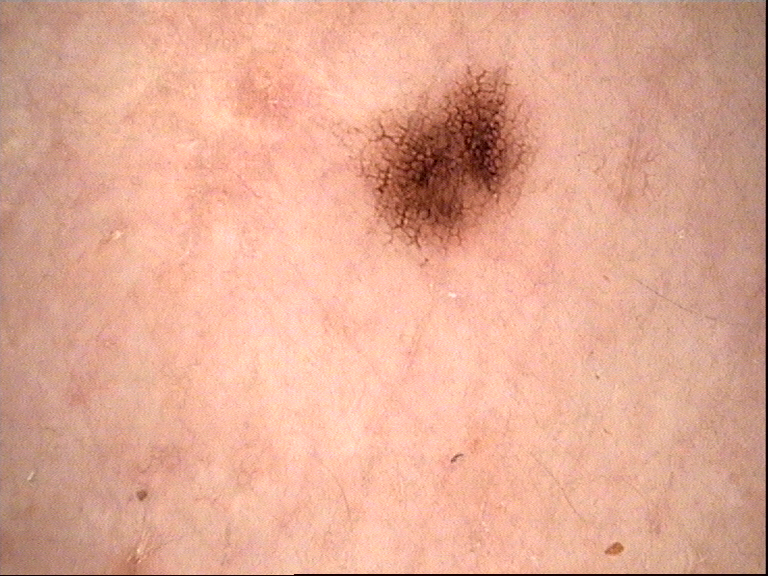Findings:
A dermoscopic photograph of a skin lesion.
Impression:
Labeled as a benign lesion — a dysplastic junctional nevus.